A close-up photograph; the leg and arm are involved: 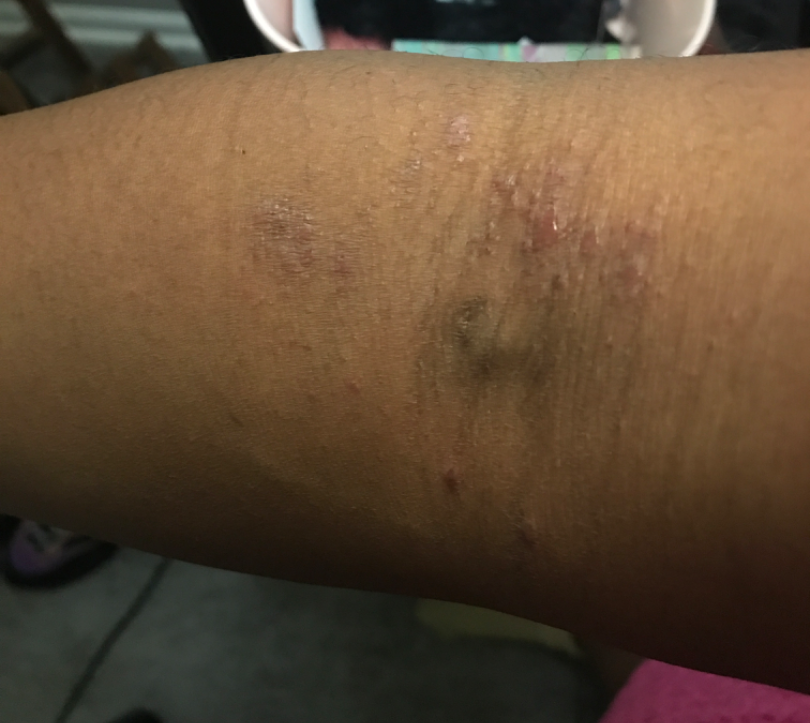clinical impression — Eczema (primary).